Dermoscopy of a skin lesion.
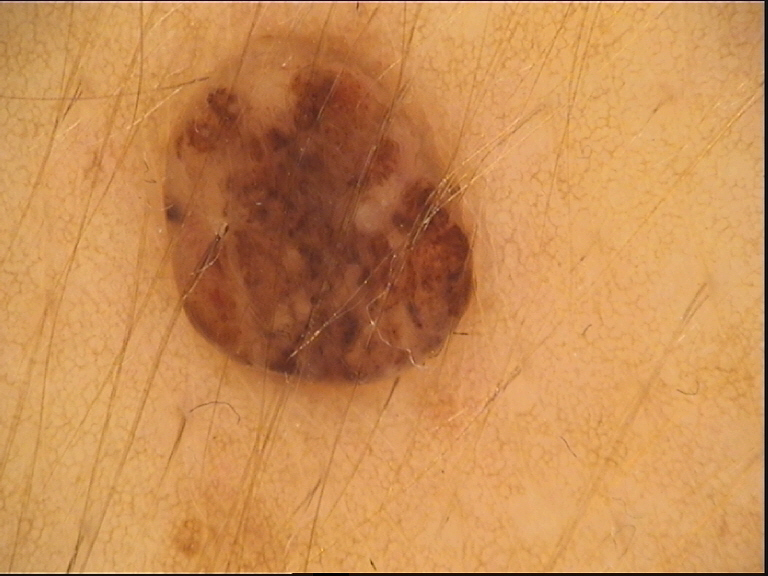The architecture is that of a banal lesion. Classified as a dermal nevus.